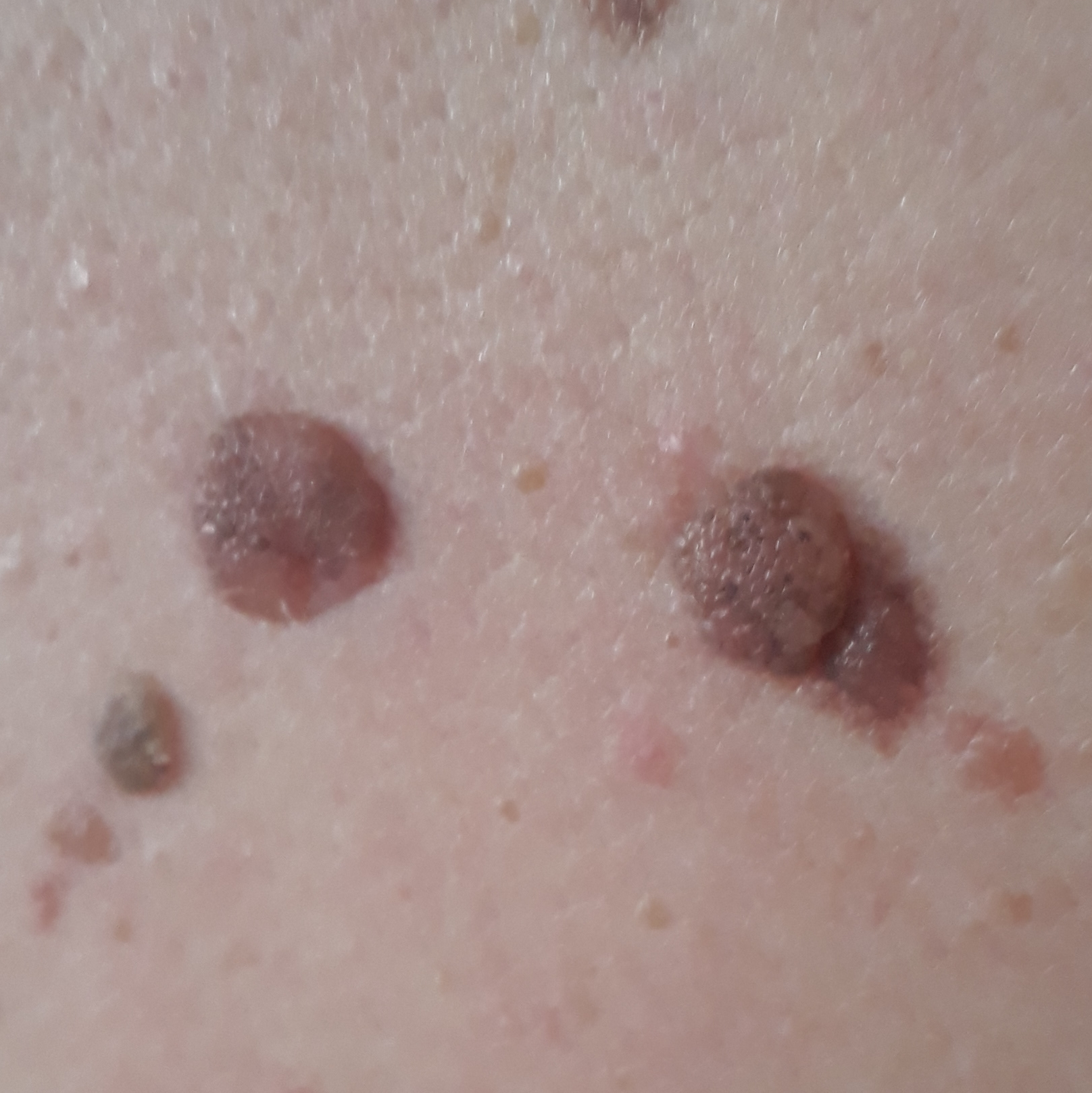  patient:
    age: 44
  image: clinical photo
  lesion_location: the back
  symptoms:
    present:
      - pain
      - elevation
    absent:
      - change in appearance
      - bleeding
  diagnosis:
    name: nevus
    code: NEV
    malignancy: benign
    confirmation: clinical consensus